The affected area is the arm · an image taken at an angle:
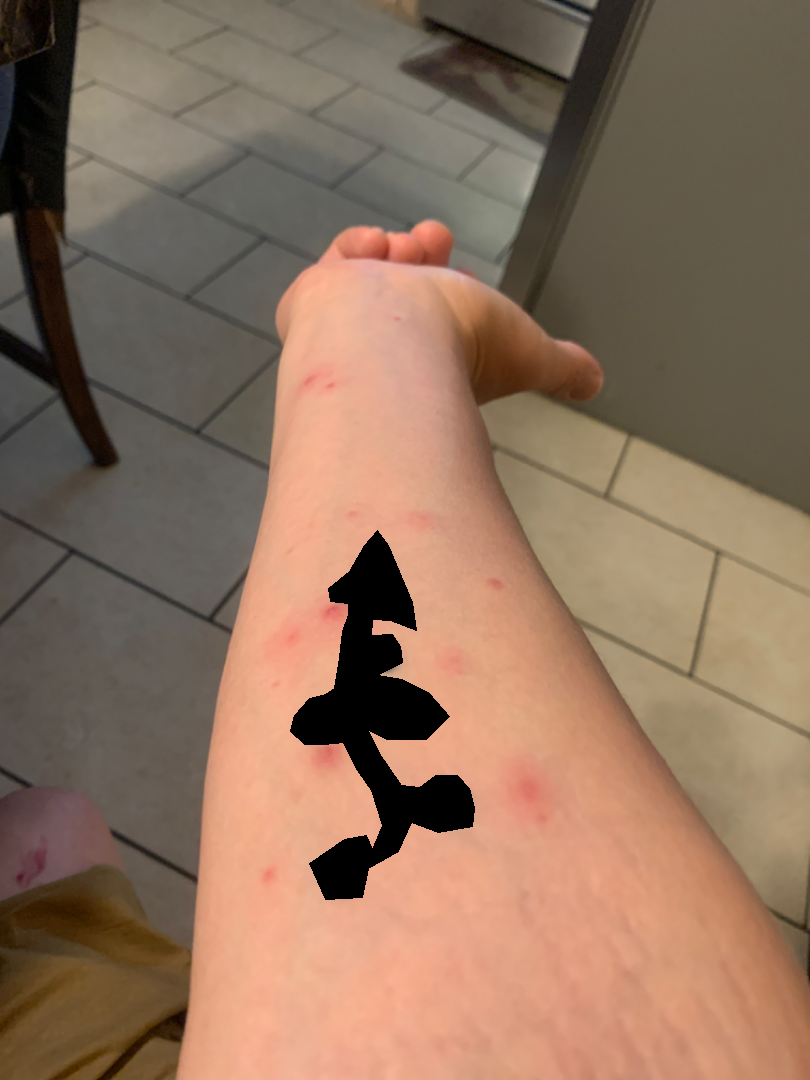self-categorized as — skin that appeared healthy to them | lesion symptoms — burning and pain | skin tone — Fitzpatrick phototype II; lay graders estimated Monk Skin Tone 2 or 3 | symptom duration — one to four weeks | clinical impression — single-reviewer assessment: the leading consideration is Insect Bite; possibly Eczema; also on the differential is Allergic Contact Dermatitis.